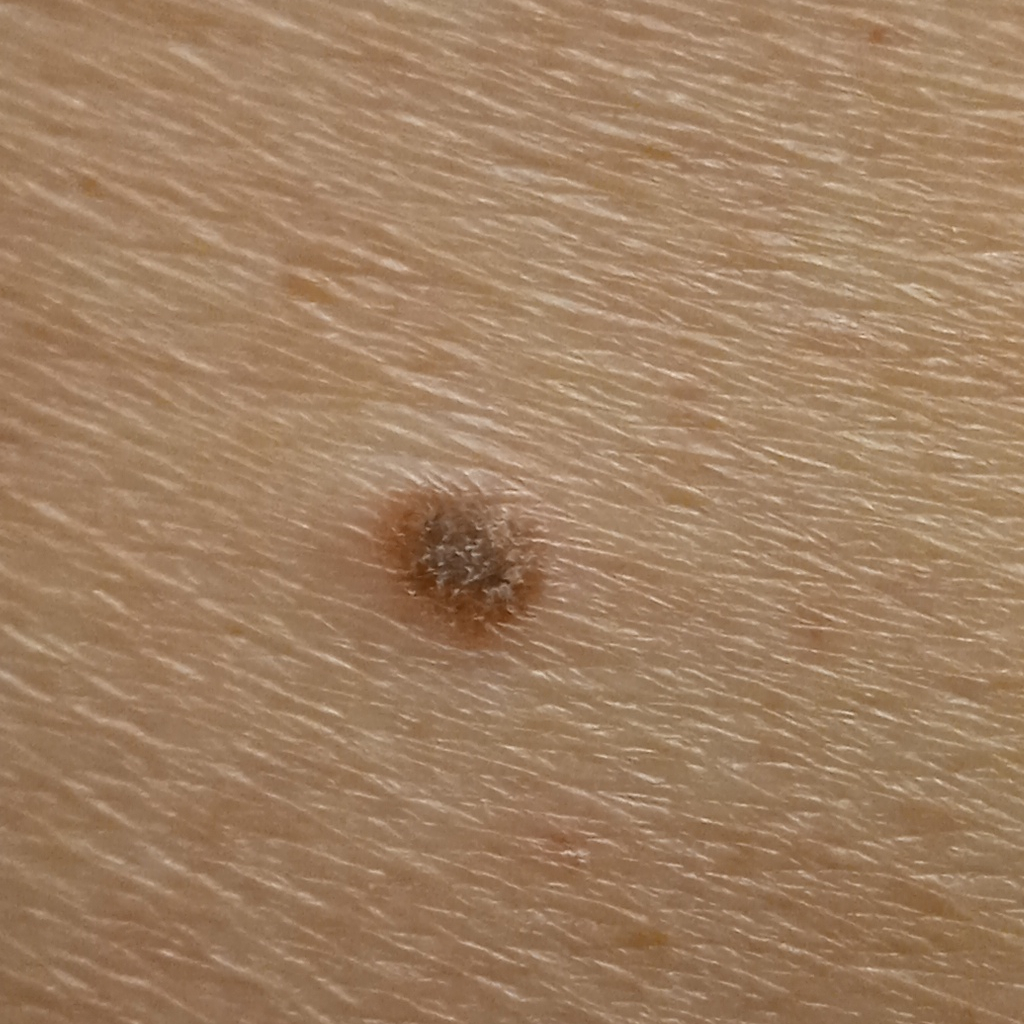Case:
– nevus count: few melanocytic nevi overall
– sun reaction: skin tans without first burning
– subject: male, aged 79
– clinical context: research study (no referral diagnosis)
– image: clinical photograph
– size: 5.9 mm
– diagnosis: seborrheic keratosis (dermatologist consensus)